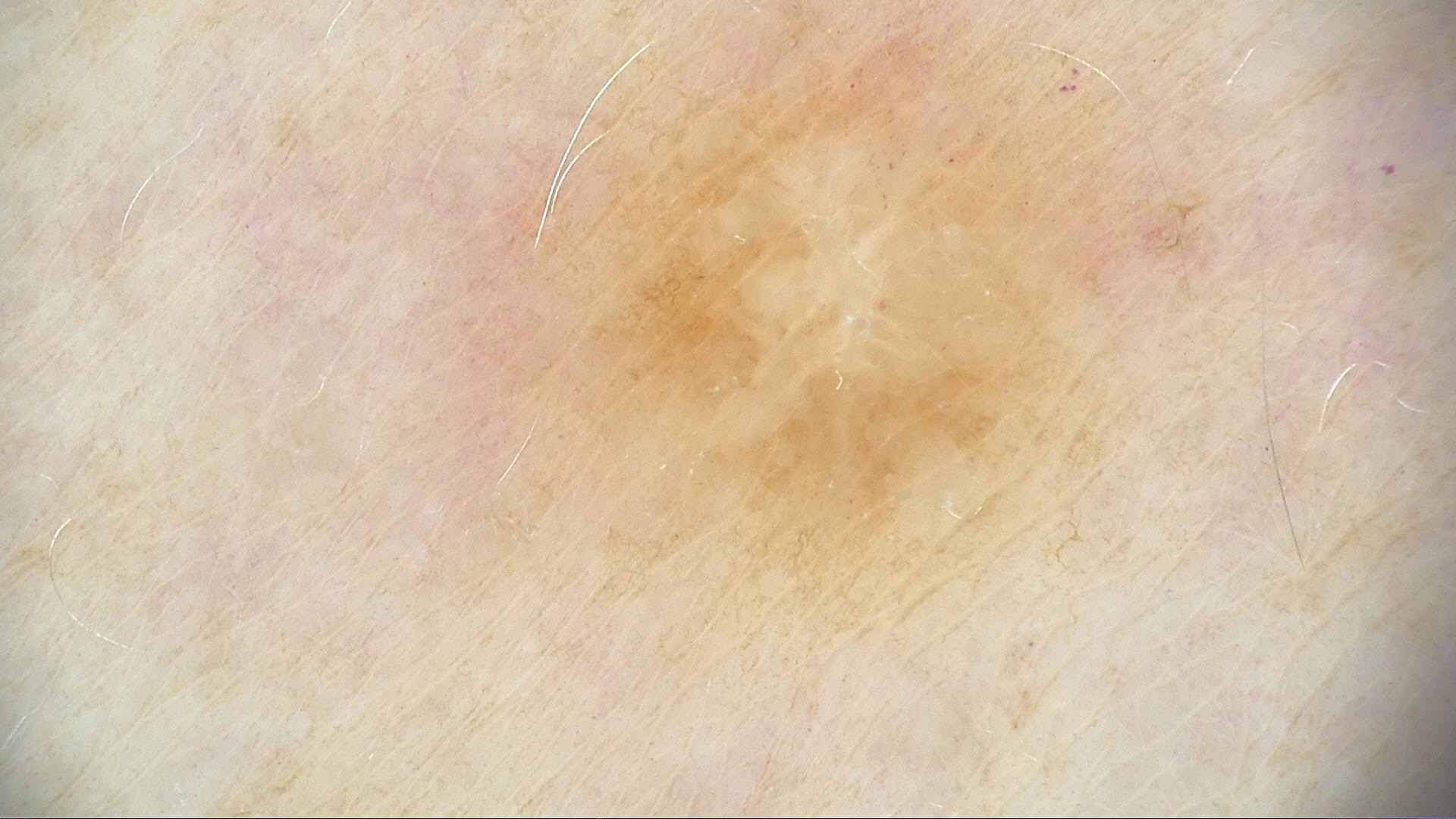Impression: Classified as a fibro-histiocytic lesion — a dermatofibroma.